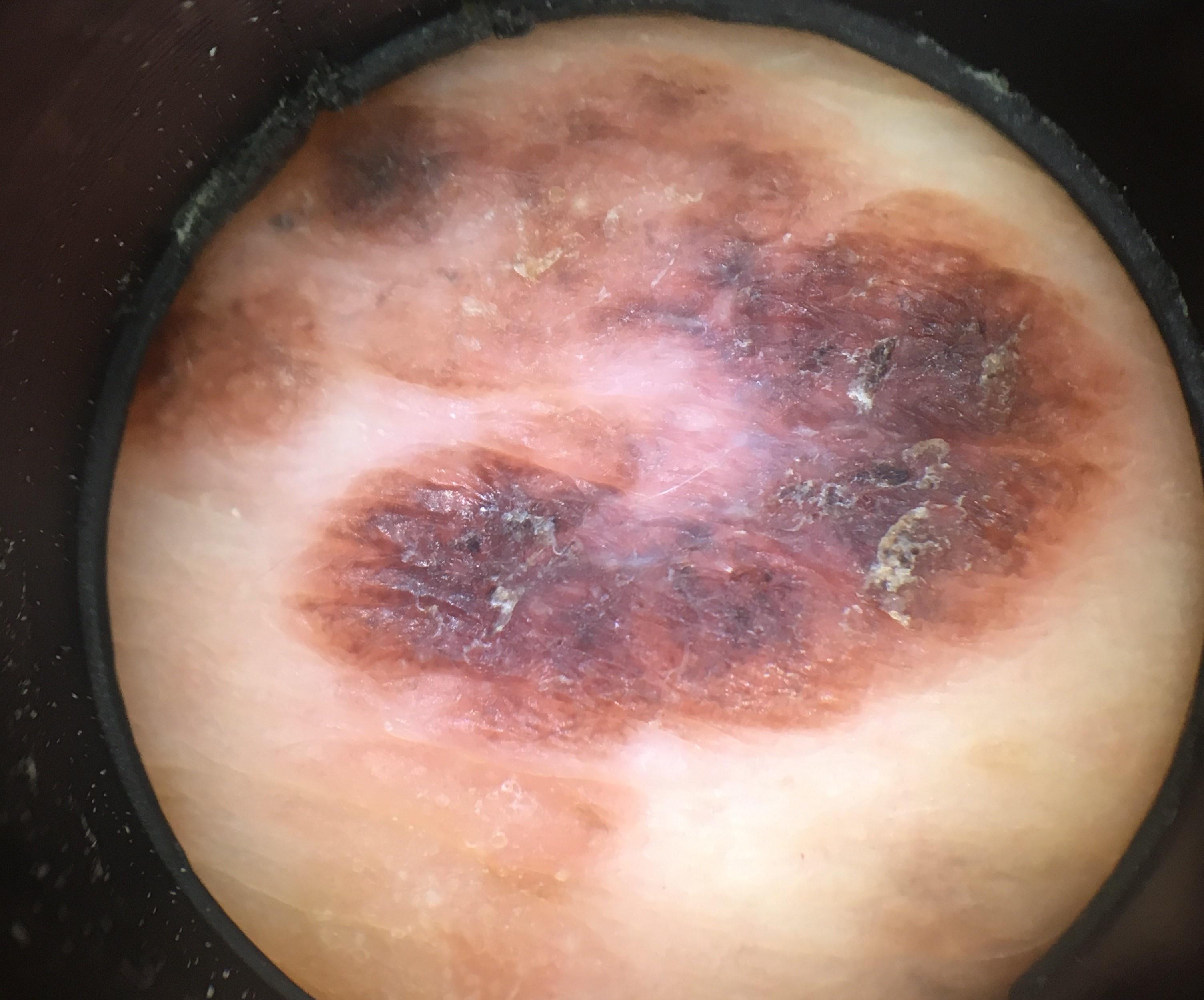Notes:
* pathology · Melanoma (biopsy-proven)